A dermoscopic photograph of a skin lesion.
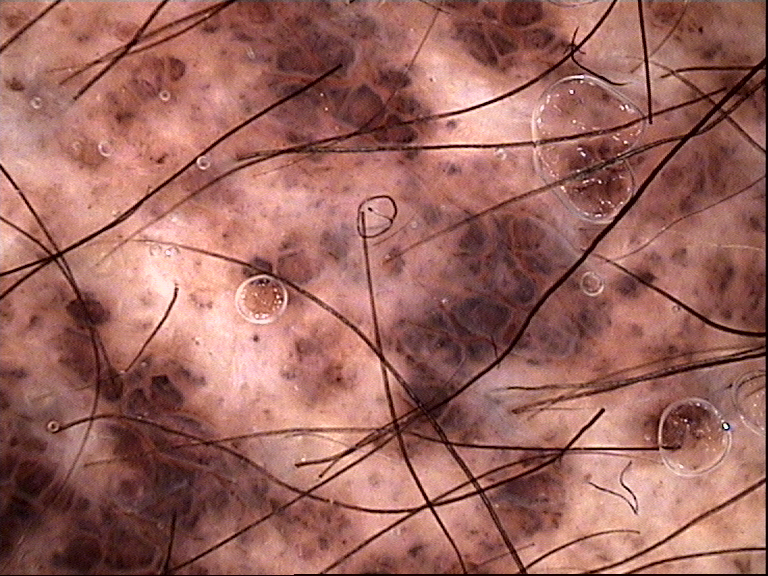Labeled as a banal lesion — a congenital compound nevus.